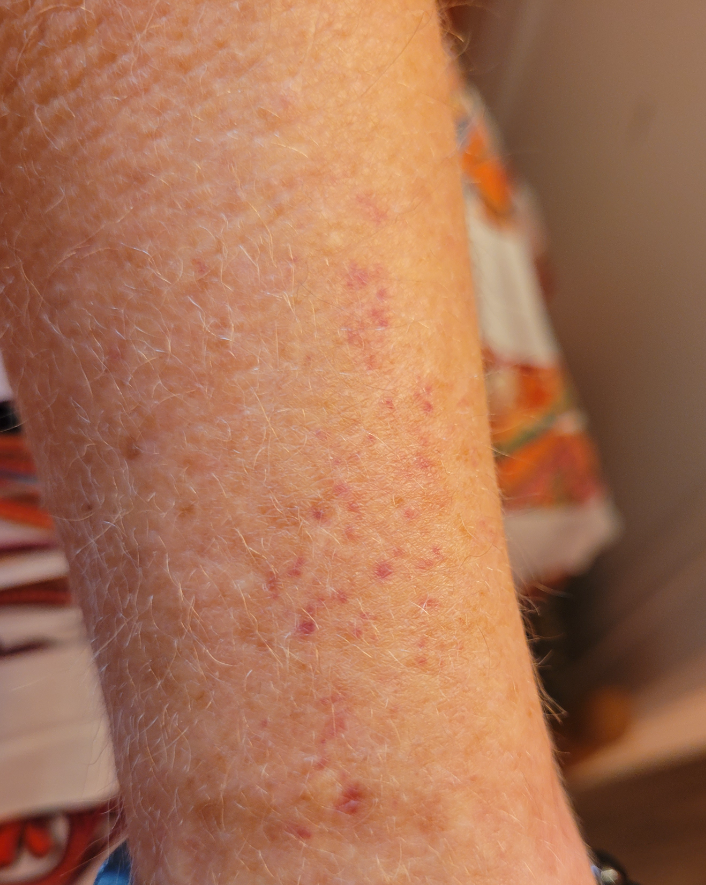The condition could not be reliably identified from the image.
Located on the arm.
The patient described the issue as a pigmentary problem.
The photograph was taken at an angle.
Reported lesion symptoms include bothersome appearance.
The lesion is described as flat.
Fitzpatrick phototype IV; lay reviewers estimated Monk Skin Tone 3 or 4.
The condition has been present for one to four weeks.